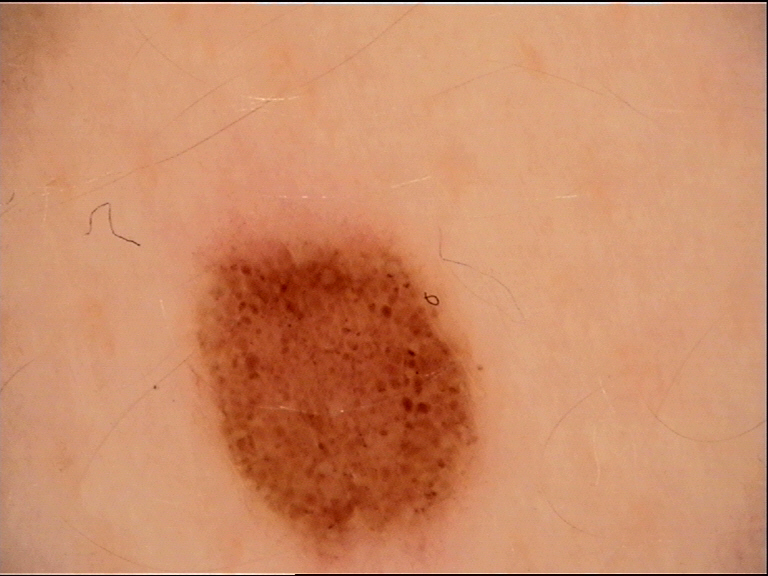Case:
– diagnostic label · junctional nevus (expert consensus)